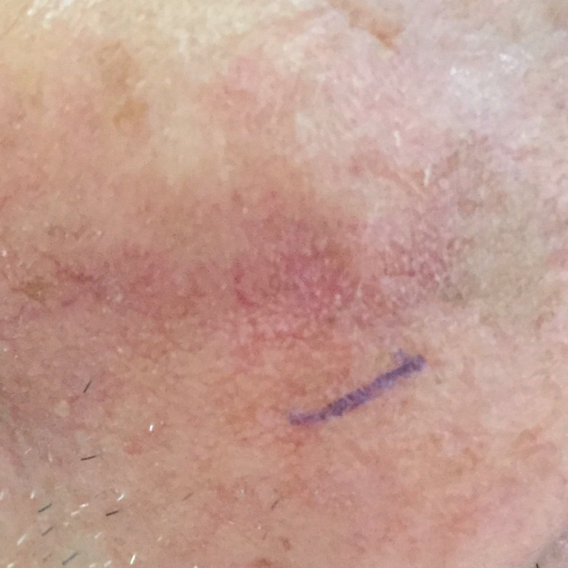Patient and lesion: A clinical photo of a skin lesion taken with a smartphone. Located on the face. Conclusion: Clinically diagnosed as an actinic keratosis.